A close-up photograph — 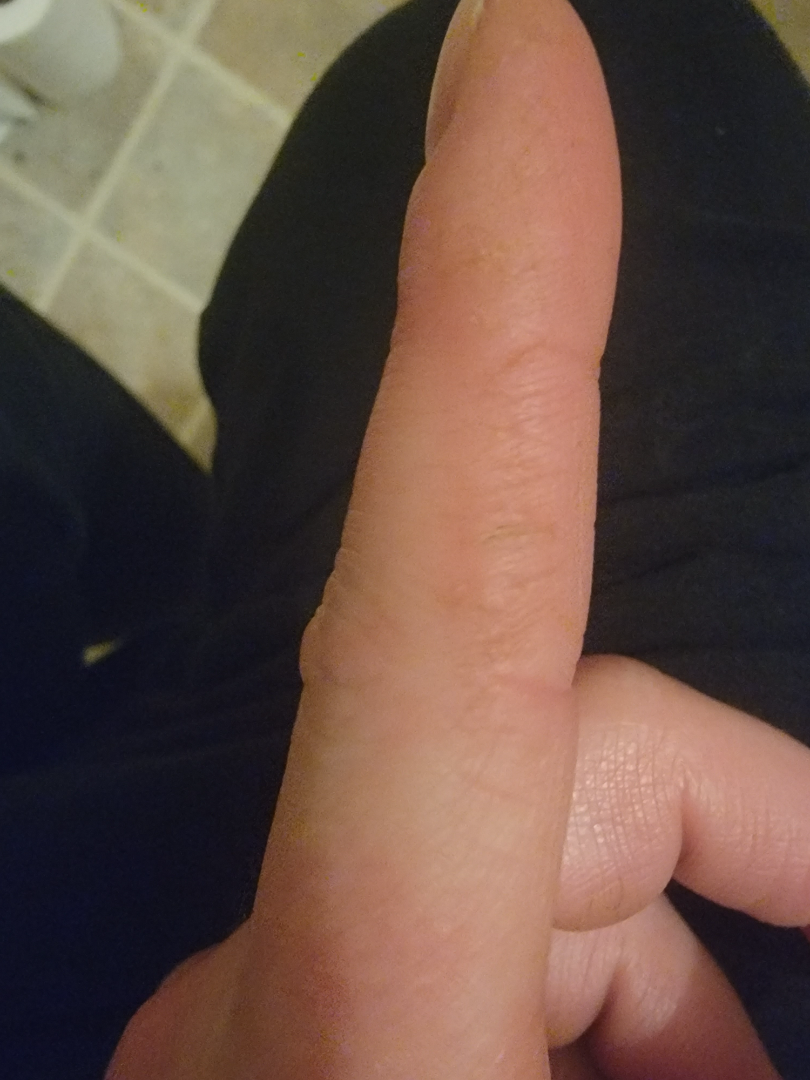The impression is Eczema.